Close-up view: 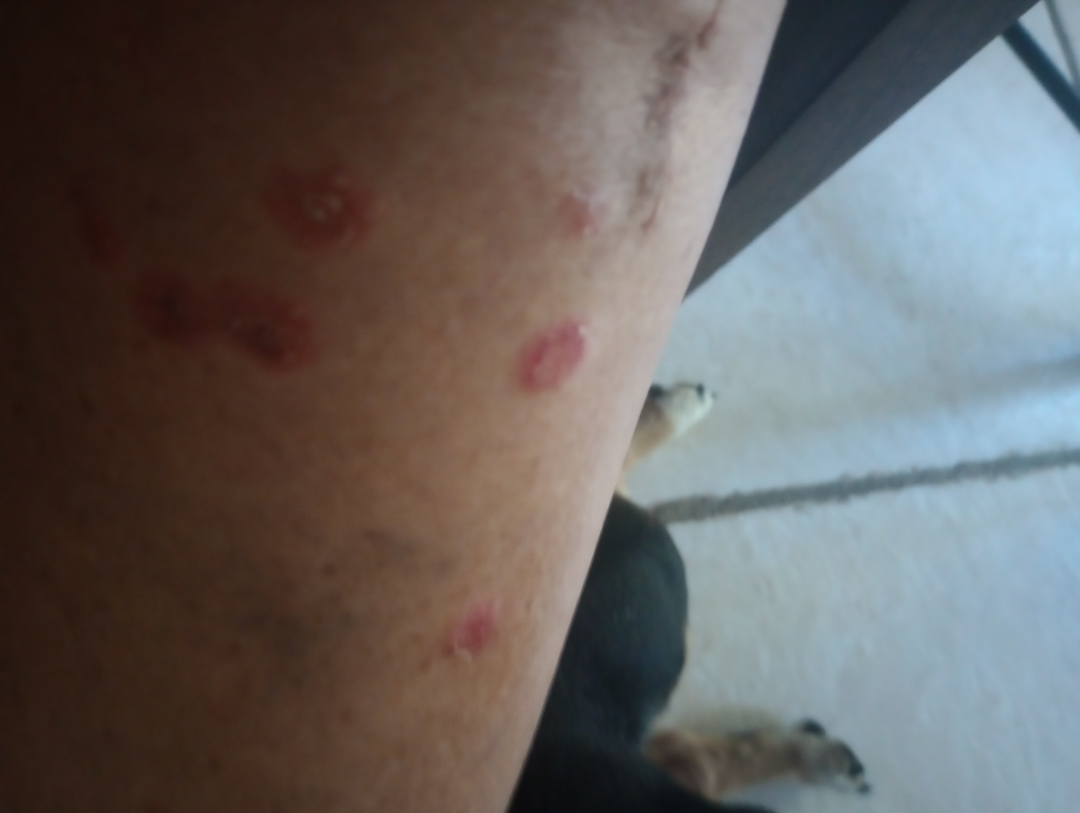Q: Could the case be diagnosed?
A: indeterminate from the photograph